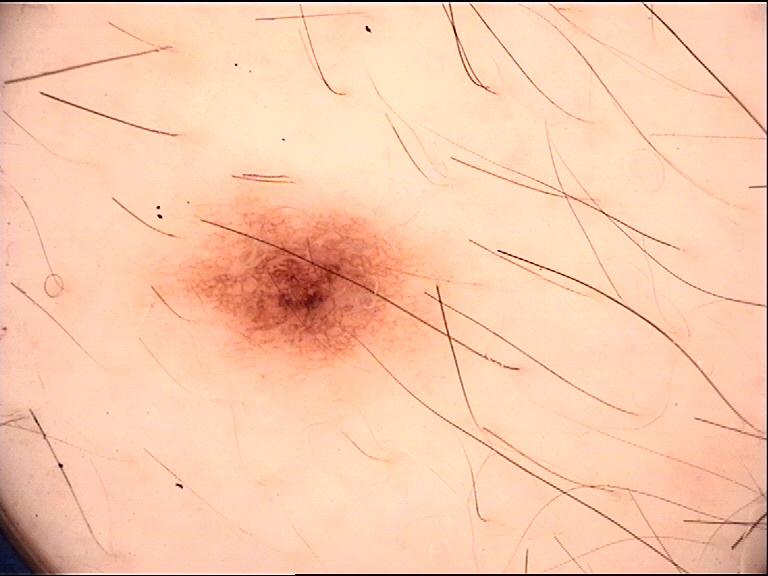image = dermatoscopy | assessment = dysplastic junctional nevus (expert consensus).